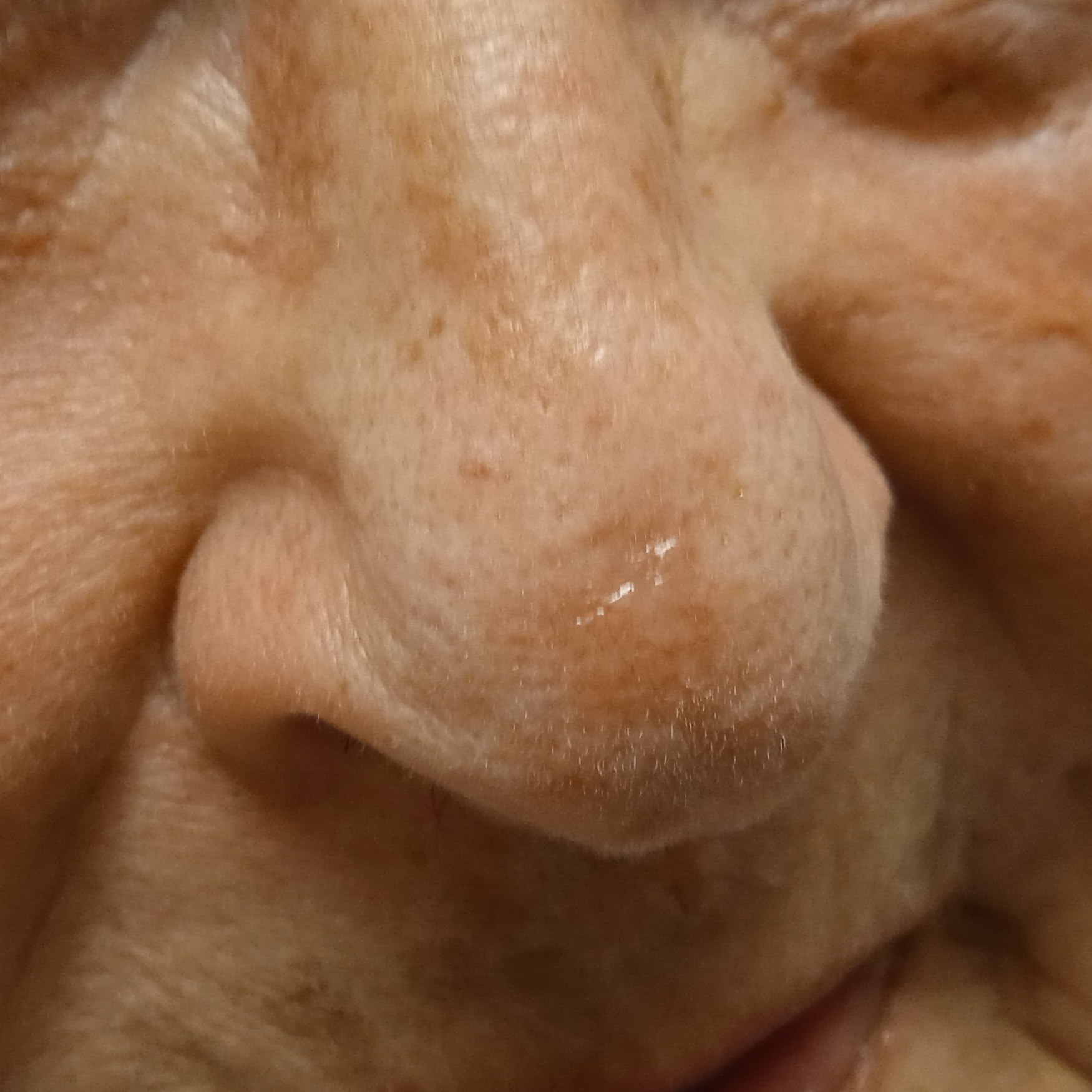{"patient": {"age": 84, "sex": "female"}, "referral": "clinical suspicion of basal cell carcinoma", "diagnosis": {"name": "basal cell carcinoma", "malignancy": "malignant", "procedure": "excision", "tumor_thickness_mm": 1.5}}